The contributor is 40–49, female. The affected area is the leg. A close-up photograph.
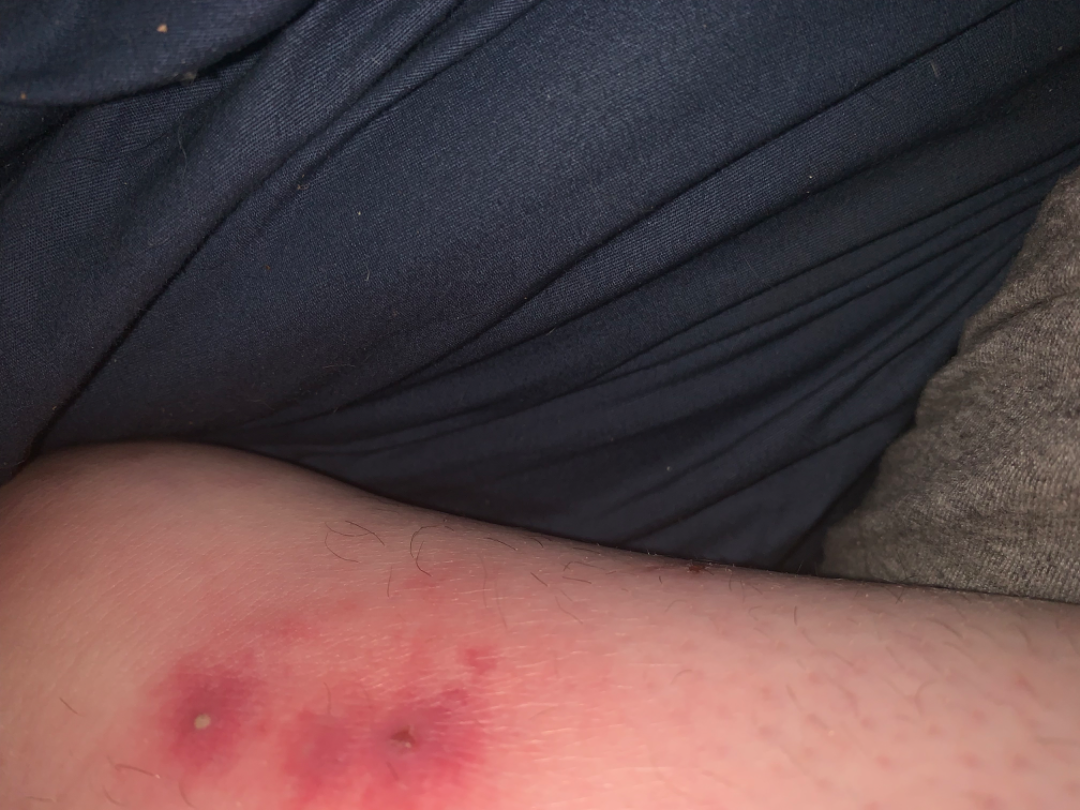Texture is reported as raised or bumpy. Associated systemic symptoms include mouth sores. Self-categorized by the patient as a rash. Present for less than one week. A single dermatologist reviewed the case: consistent with Impetigo.